The leg is involved, the photo was captured at a distance — 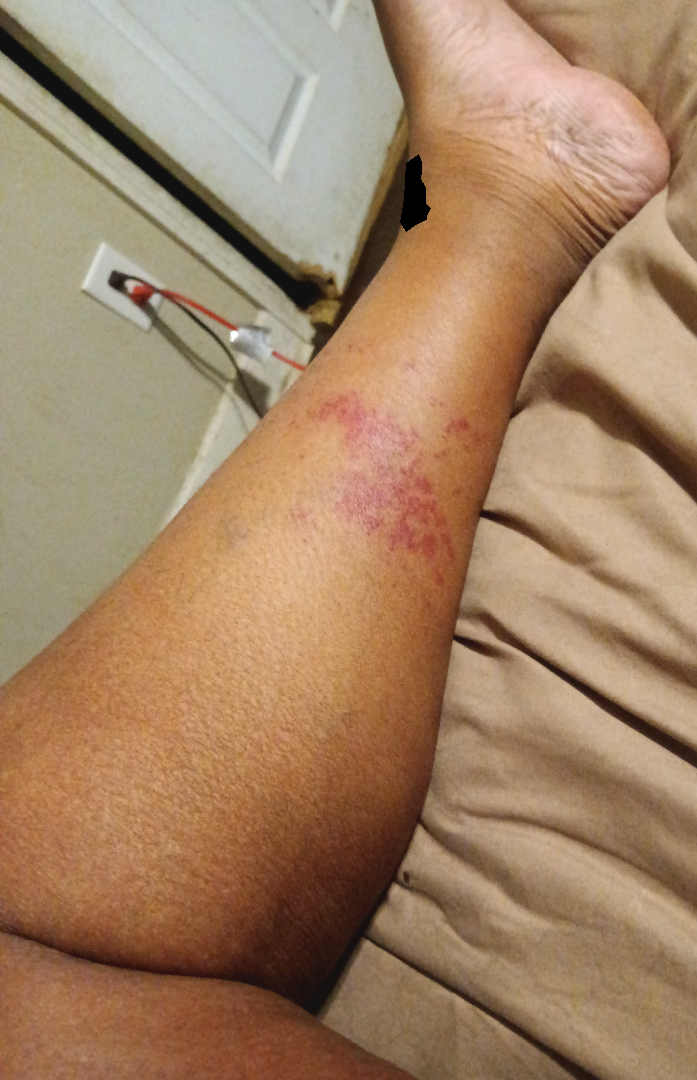assessment: indeterminate